Acquired for a research image collection, with no referral diagnosis · a male patient 60 years old — 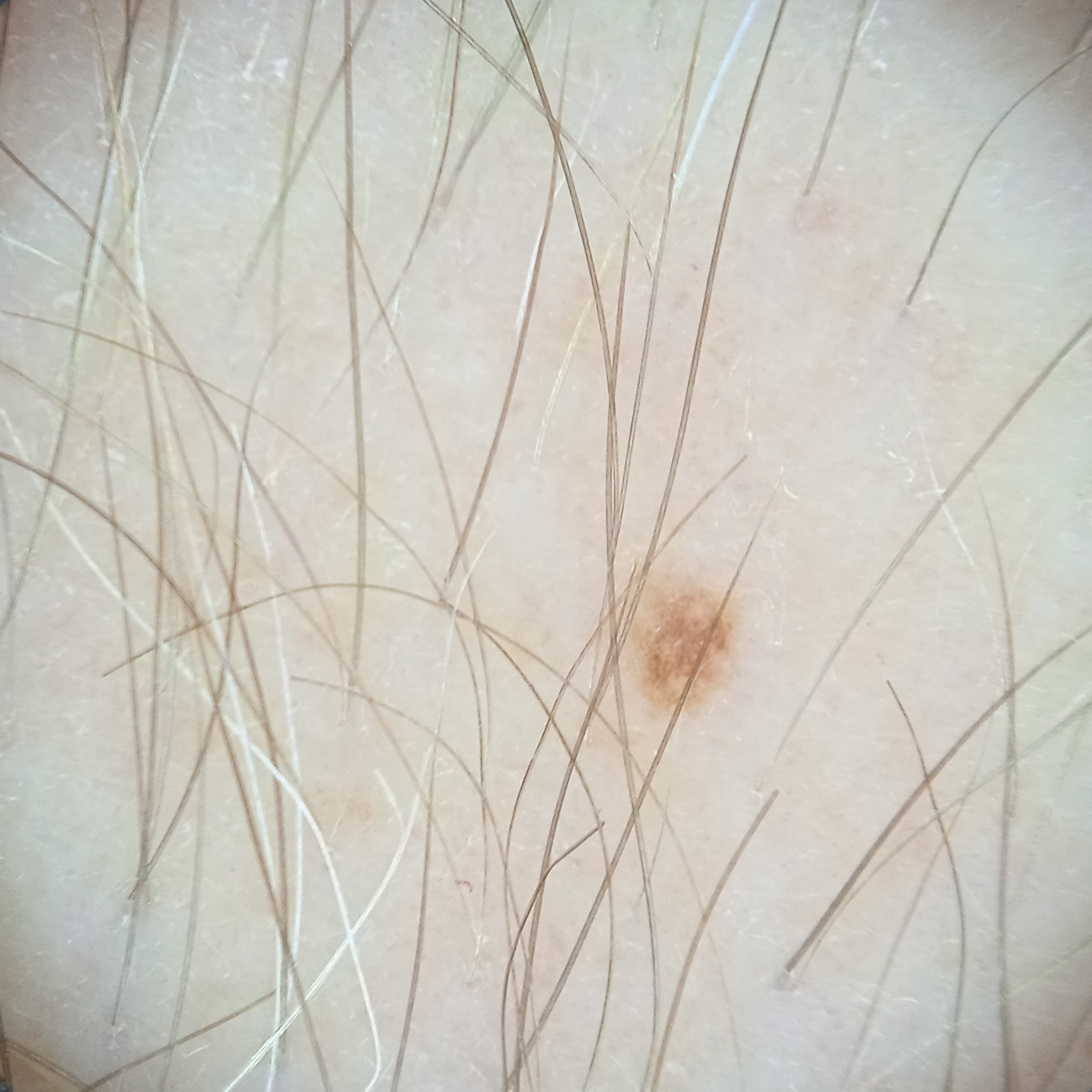body site = an arm | diameter = 1.5 mm | assessment = melanocytic nevus (dermatologist consensus).